Close-up view; located on the head or neck: 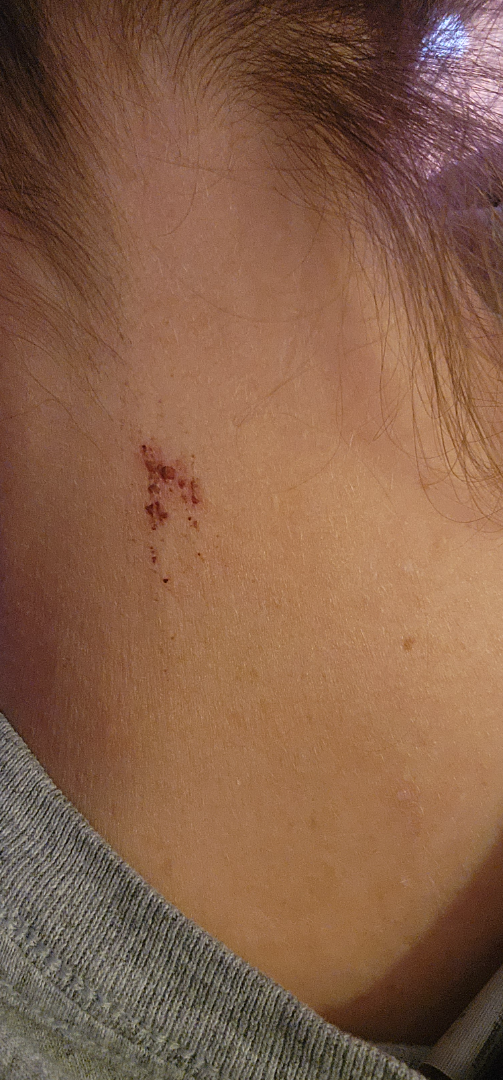<report>
  <differential>
    <leading>Abrasion, scrape, or scab</leading>
    <considered>Inflicted skin lesions</considered>
    <unlikely>Infection of skin</unlikely>
  </differential>
</report>